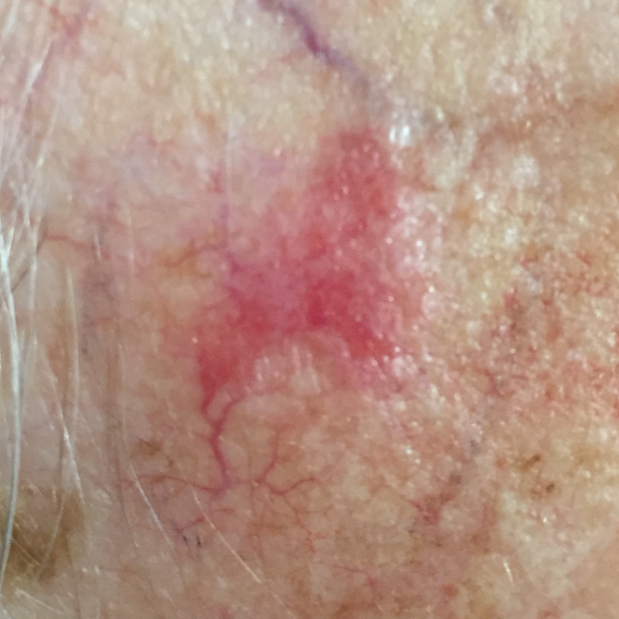patient: female, in their late 80s; body site: the face; patient-reported symptoms: itching, growth / no pain; diagnosis: basal cell carcinoma (biopsy-proven).